A dermoscopic image of a skin lesion: 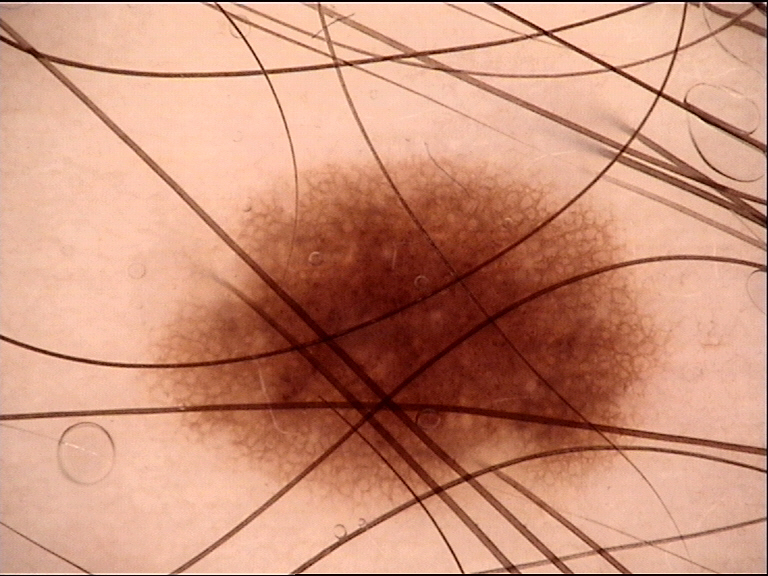label=dysplastic junctional nevus (expert consensus).